Collected as part of a research study, without a referral diagnosis · dermoscopy of a skin lesion · a male patient aged 83.
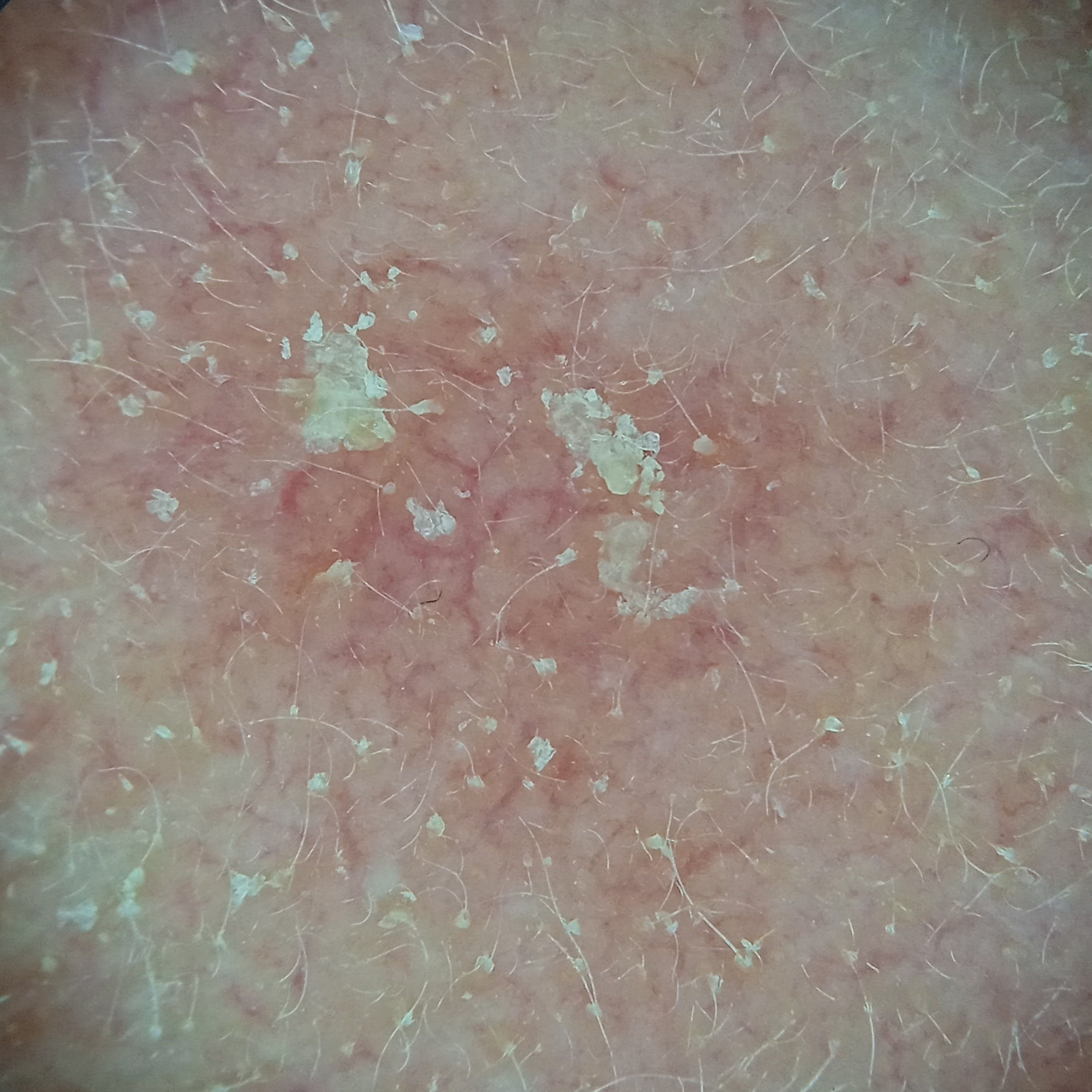<case>
<diagnosis>
<name>actinic keratosis</name>
<malignancy>benign</malignancy>
</diagnosis>
</case>